This is a close-up image.
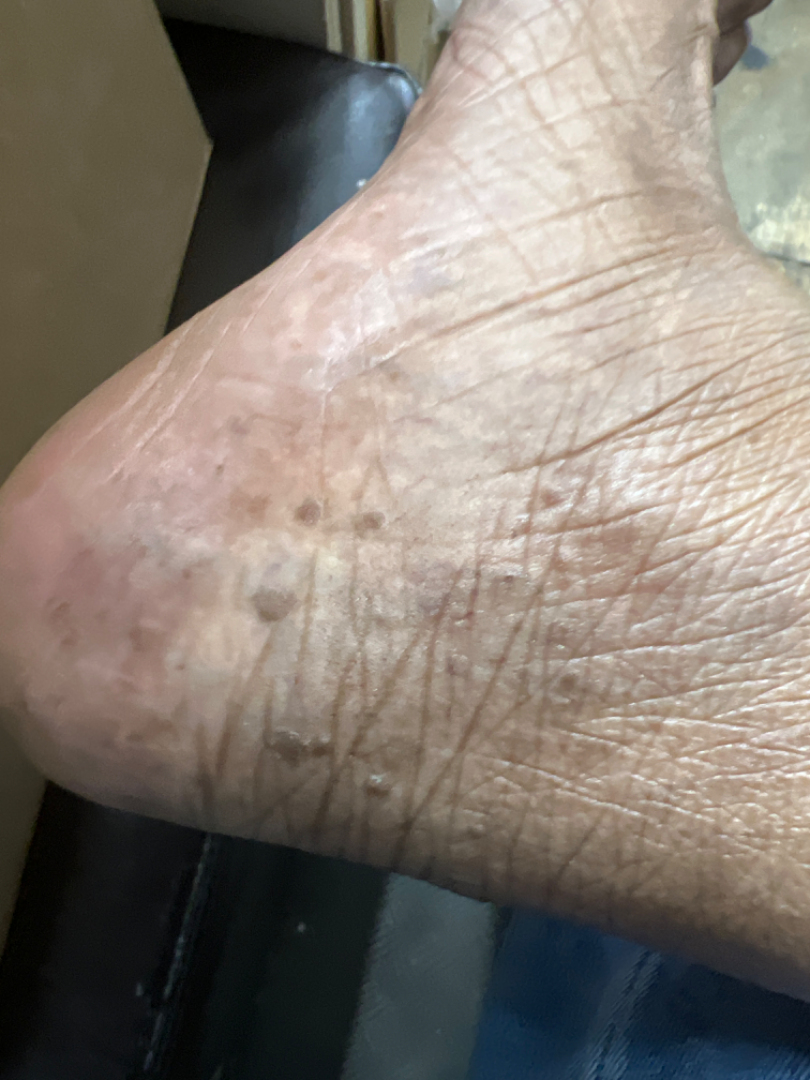Impression: On remote review of the image: consistent with SK/ISK.